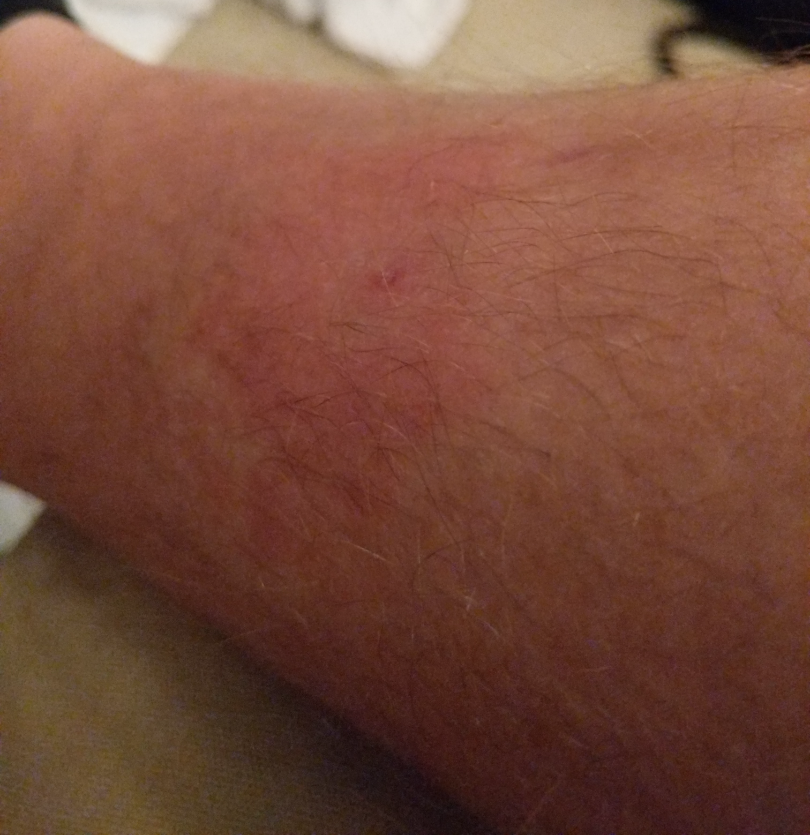image framing — at an angle | constitutional symptoms — none reported | present for — less than one week | contributor — male, age 30–39 | symptoms — enlargement and itching | texture — flat | body site — leg | clinical impression — one reviewing dermatologist: the leading consideration is Insect Bite; also on the differential is Localized skin infection; also raised was Allergic Contact Dermatitis.